A patient in their 60s.
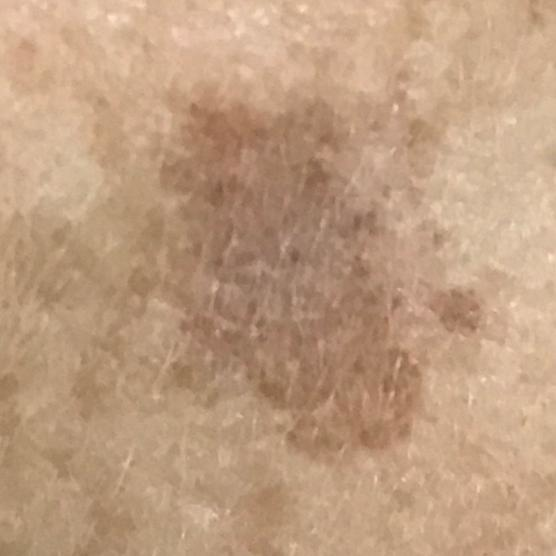The lesion is located on the face. The patient describes that the lesion has not bled and does not itch. The diagnostic impression was a seborrheic keratosis.